A female patient 78 years old. The patient says their skin tans without first burning. Acquired for a research image collection, with no referral diagnosis. A skin lesion imaged with a dermatoscope:
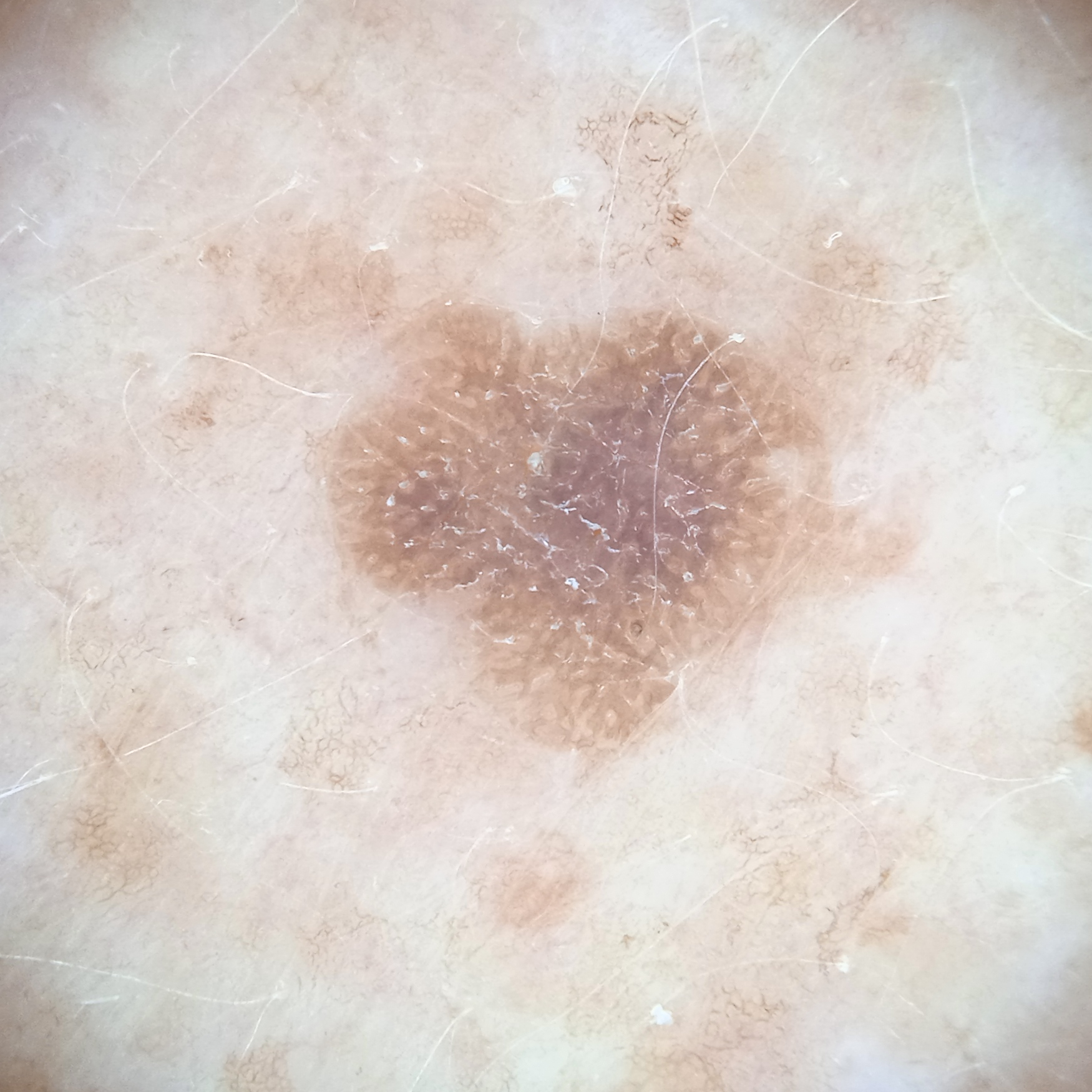body site: the back; diameter: 5.6 mm; assessment: seborrheic keratosis (dermatologist consensus).